Associated systemic symptoms include fatigue and shortness of breath · the photograph was taken at an angle · reported duration is more than five years · the patient is 30–39, female · the lesion is described as raised or bumpy · symptoms reported: enlargement, bothersome appearance and itching — 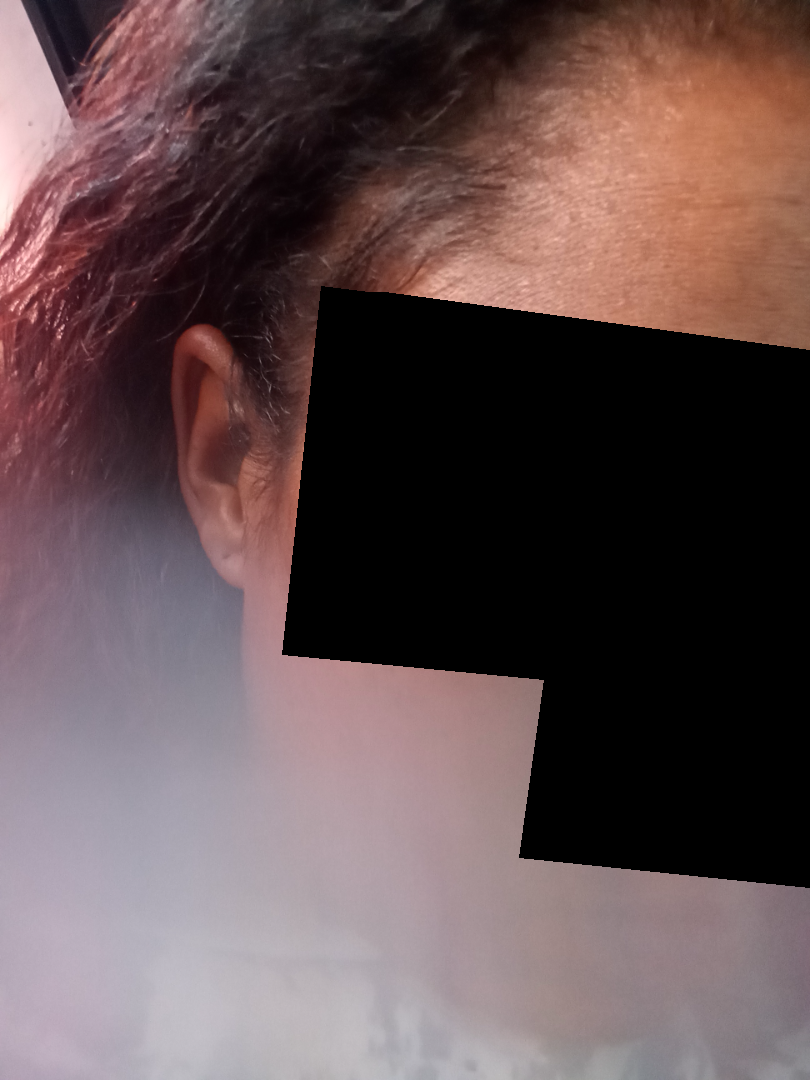The case was difficult to assess from the available photograph.